The photograph is a close-up of the affected area.
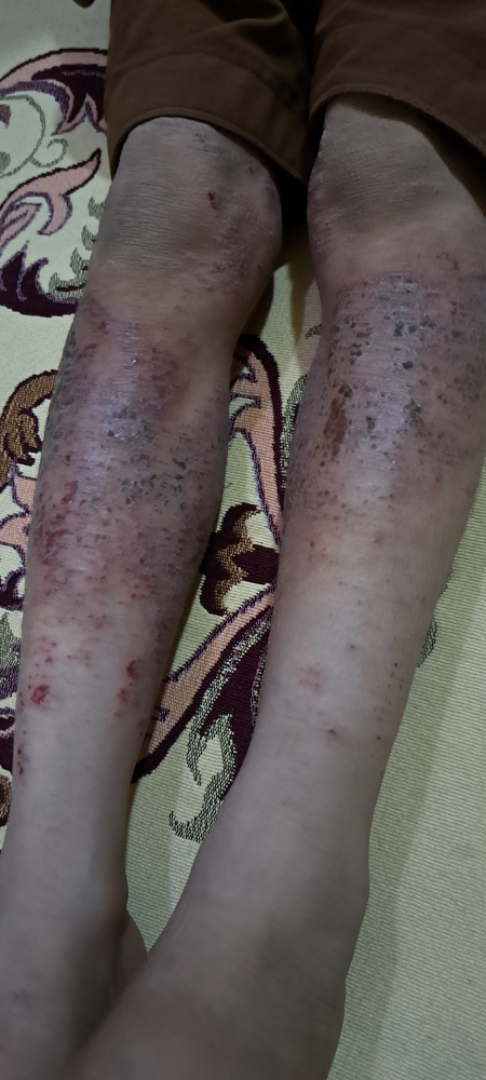Findings:
* skin tone: Fitzpatrick phototype V
* assessment: the leading impression is Infected eczema